Dermoscopy of a skin lesion.
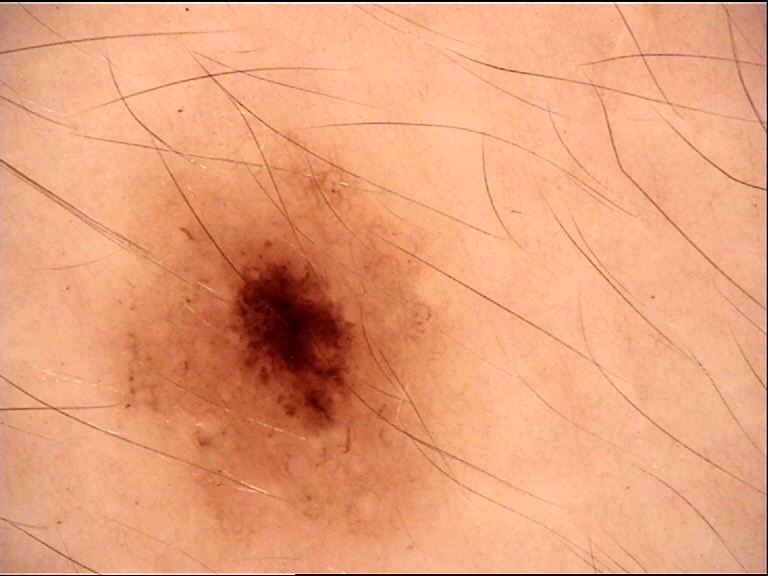Diagnosed as a benign lesion — a dysplastic compound nevus.